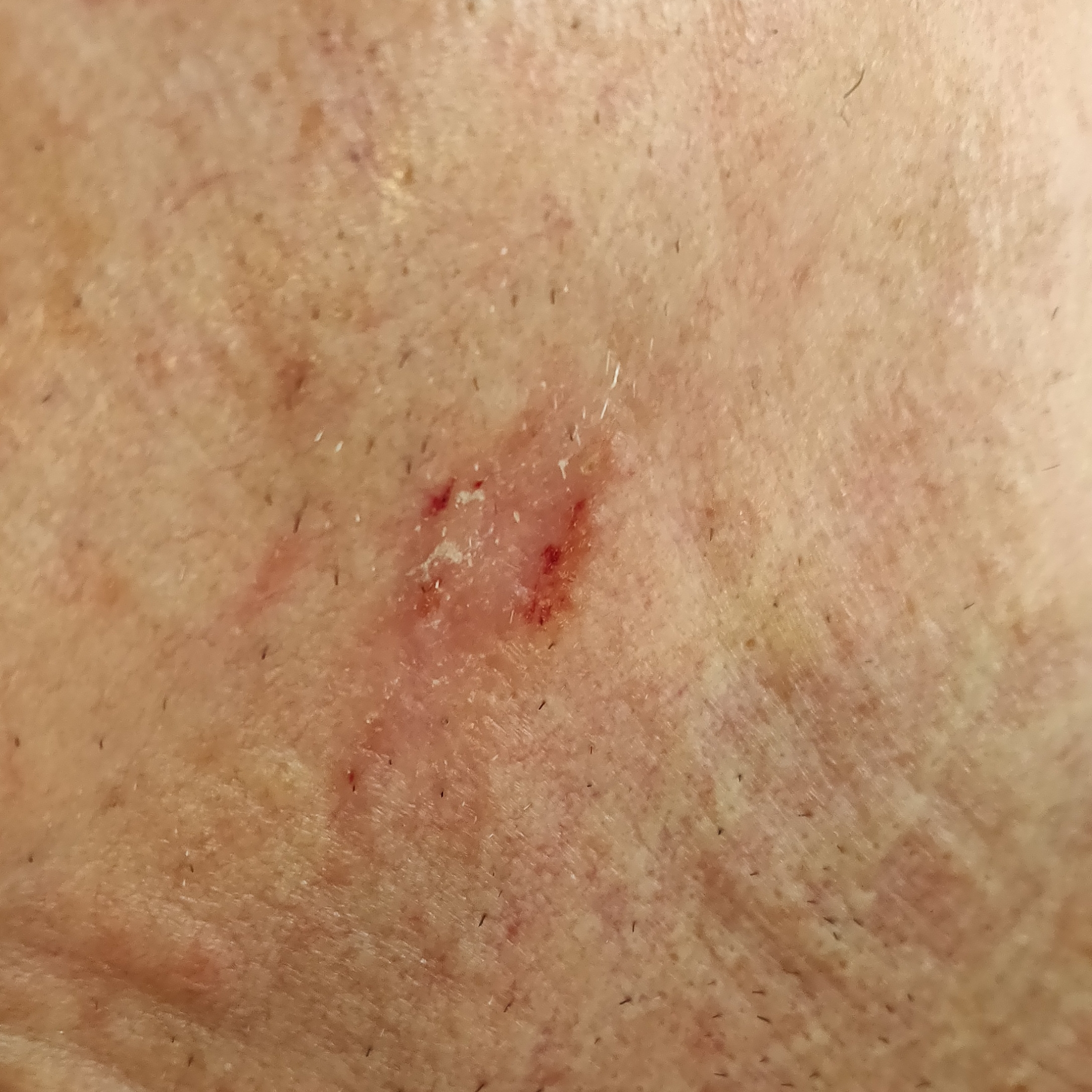{"image": "clinical photo", "skin_type": "II", "risk_factors": {"positive": ["prior cancer (patient or family)", "alcohol use", "prior skin cancer (patient or family)"], "negative": ["smoking", "pesticide exposure"]}, "lesion_location": "the neck", "lesion_size": {"diameter_1_mm": 11.0, "diameter_2_mm": 10.0}, "symptoms": {"present": ["itching", "growth"]}, "diagnosis": {"name": "actinic keratosis", "code": "ACK", "malignancy": "indeterminate", "confirmation": "clinical consensus"}}